A clinical photo of a skin lesion taken with a smartphone; a subject in their 60s — 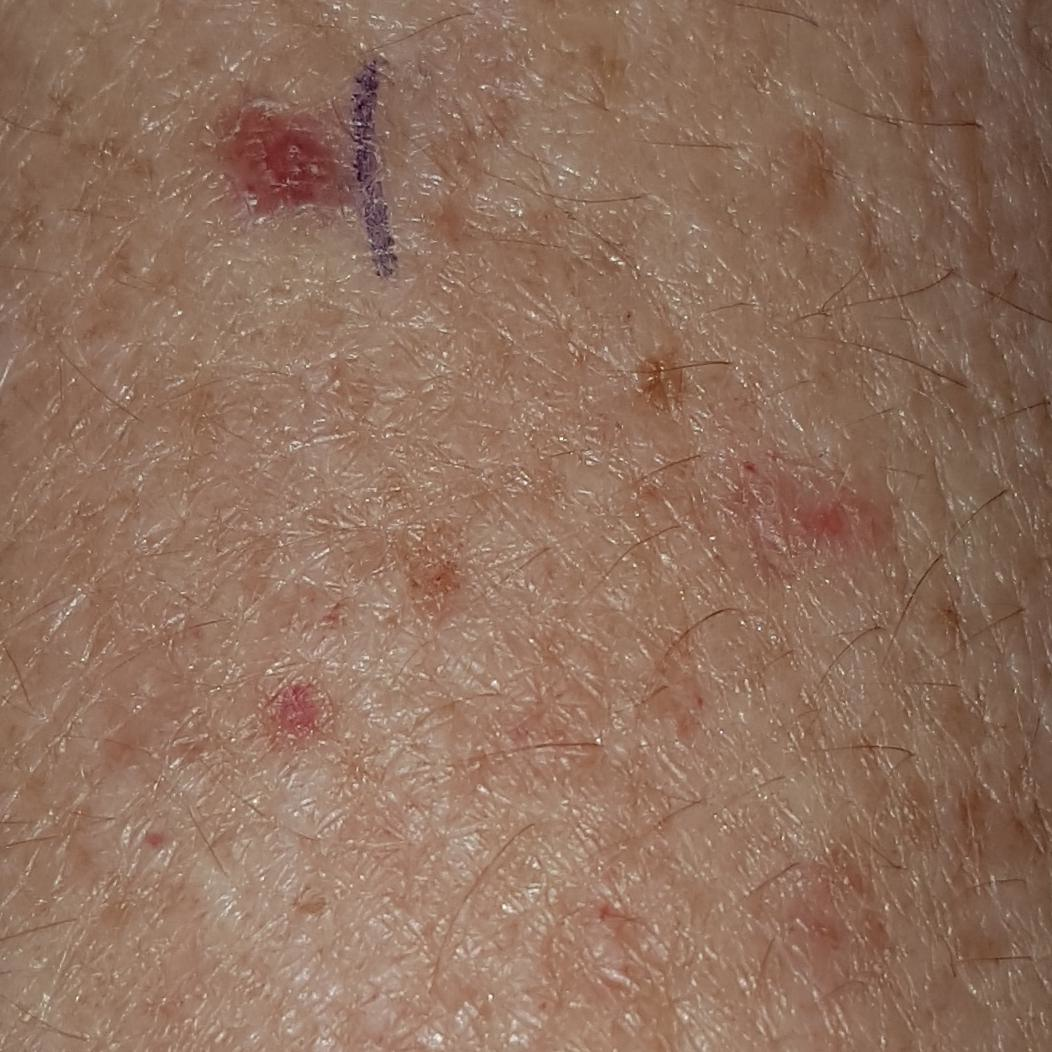Findings:
The lesion was found on a forearm. The patient describes that the lesion has grown and itches, but has not bled and is not elevated.
Conclusion:
Clinically diagnosed as a lesion of indeterminate malignant potential — an actinic keratosis.